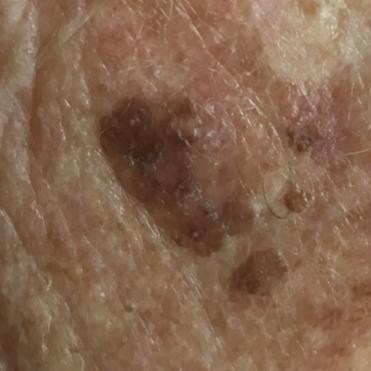– subject · in their 70s
– image · smartphone clinical photo
– site · the face
– impression · seborrheic keratosis (clinical consensus)